A dermoscopic image of a skin lesion.
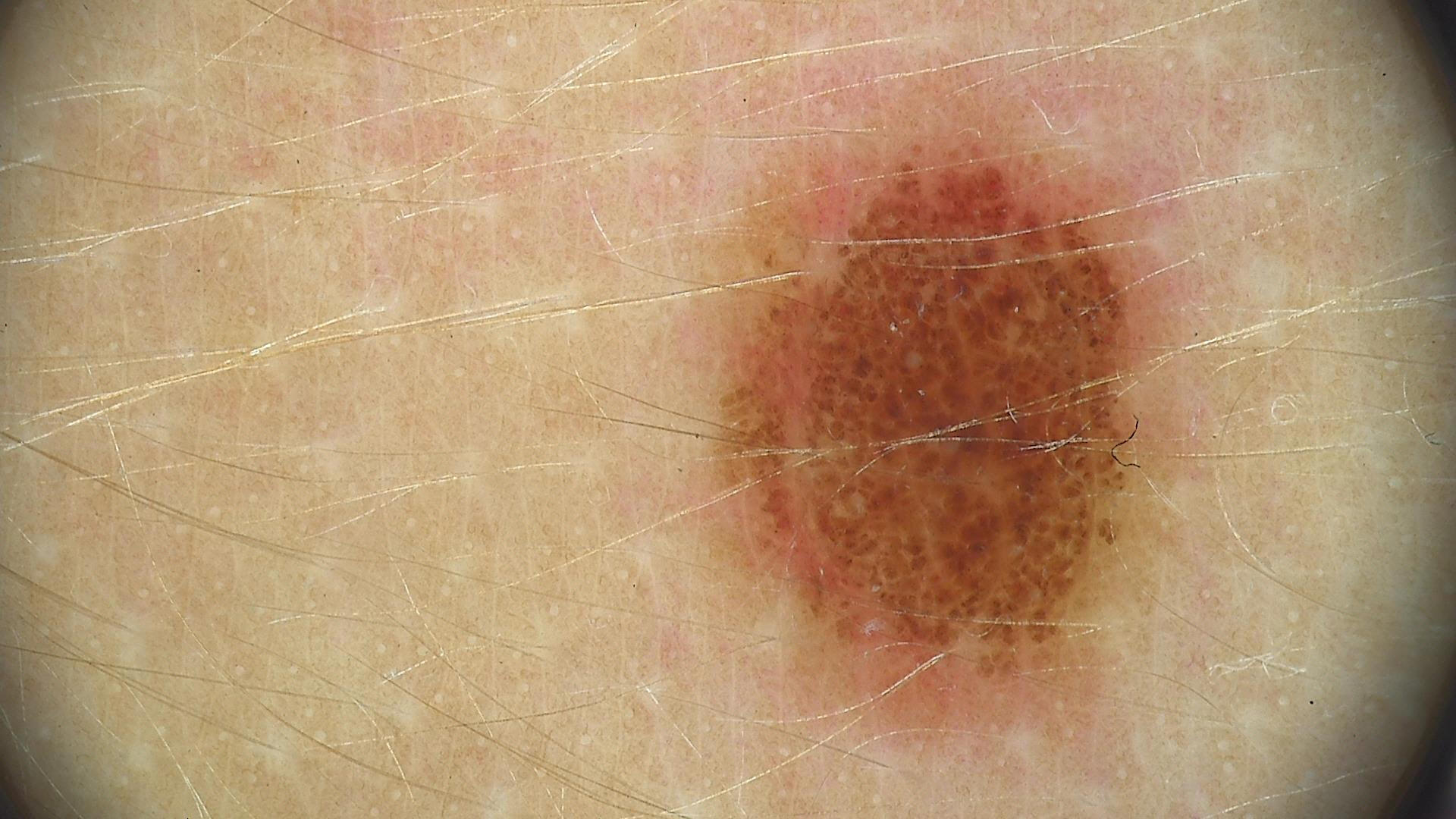The diagnosis was a dysplastic junctional nevus.